Located on the back of the hand. Self-categorized by the patient as a rash. No constitutional symptoms were reported. The contributor notes itching. Reported duration is about one day. The subject is 18–29, female. The lesion is described as fluid-filled. Close-up view — 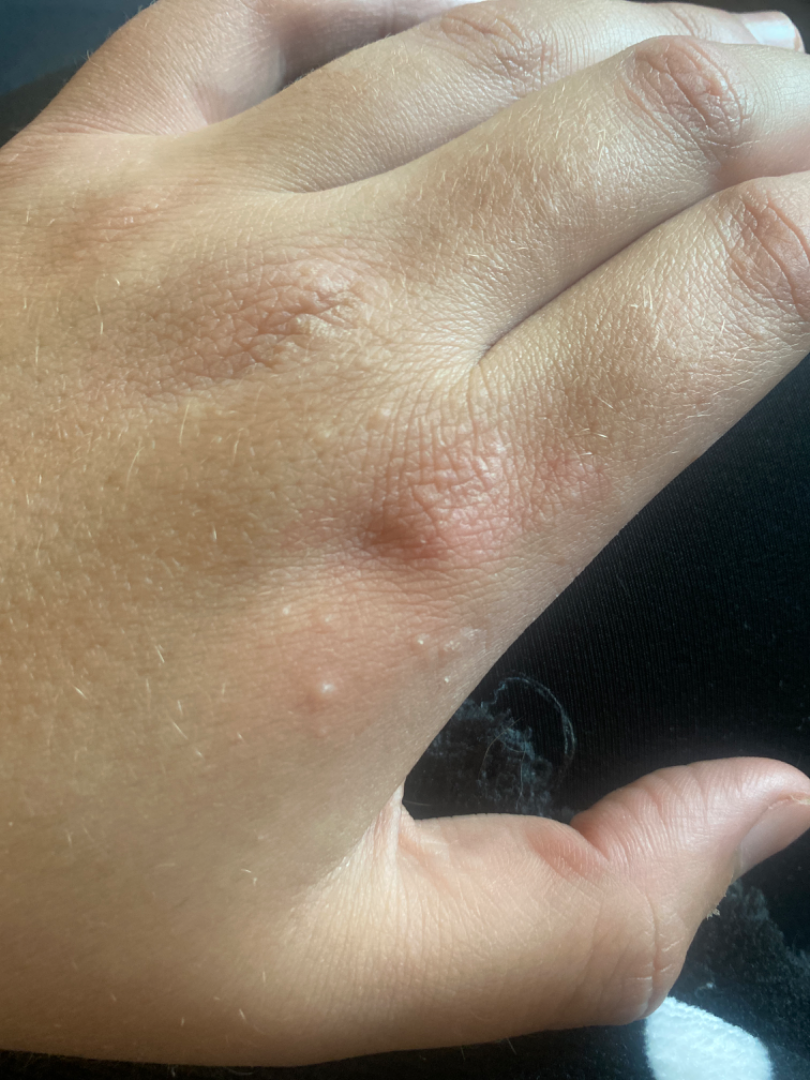| field | value |
|---|---|
| assessment | ungradable on photographic review |